The contributor is a female aged 30–39 · the contributor notes the lesion is raised or bumpy and rough or flaky · located on the head or neck · symptoms reported: enlargement, bothersome appearance, bleeding and itching · the photo was captured at an angle.
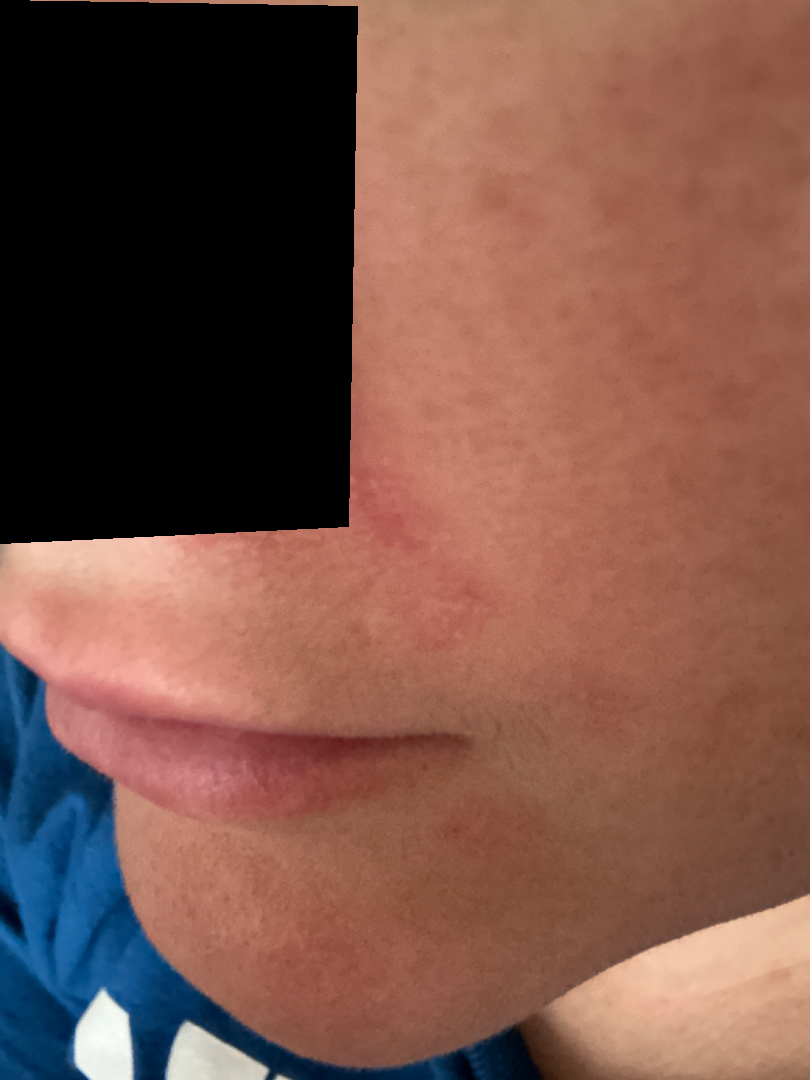differential diagnosis = reviewed remotely by one dermatologist: most consistent with Perioral Dermatitis.